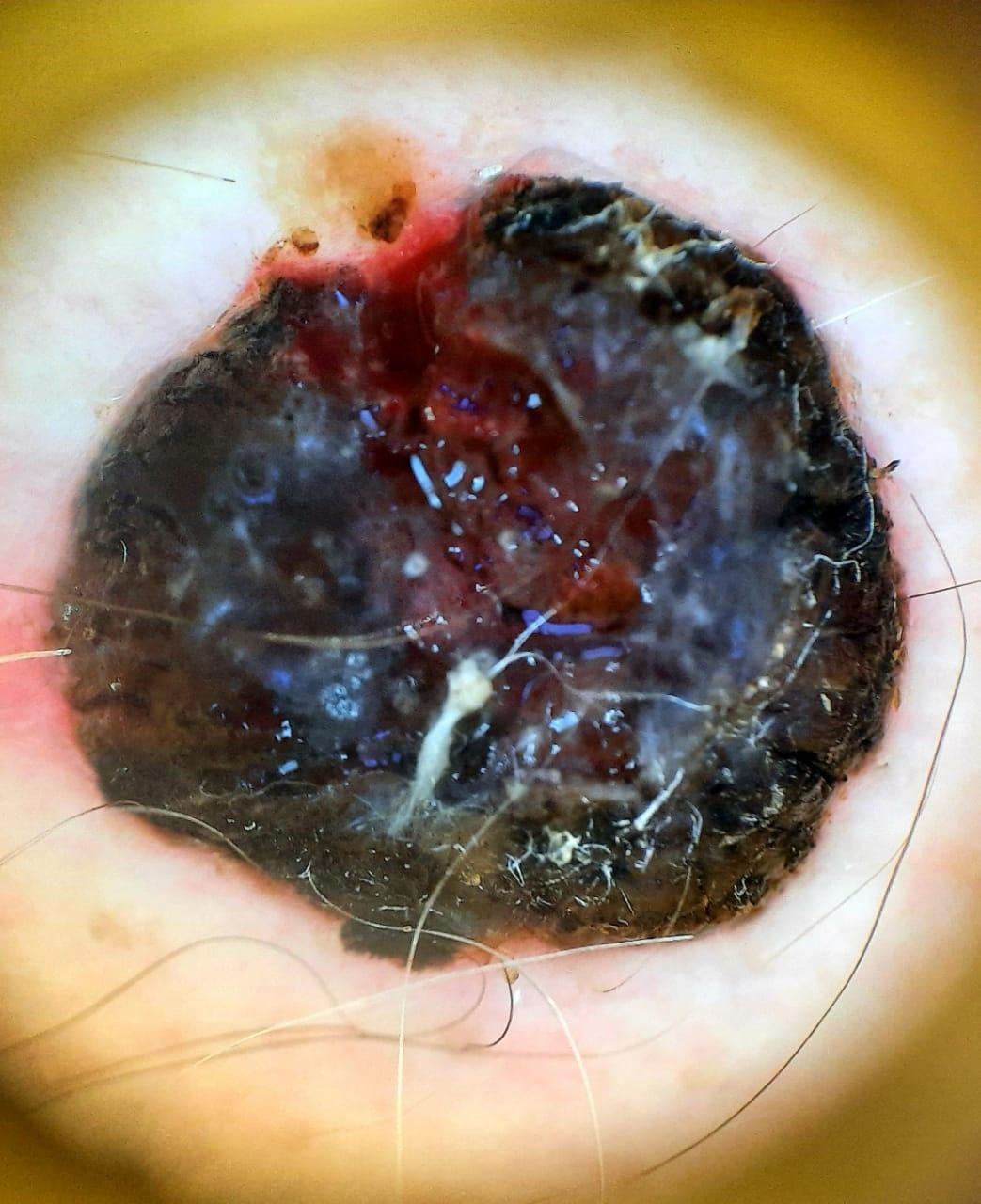A male patient about 75 years old. A dermatoscopic image of a skin lesion. Recorded as Fitzpatrick II. On biopsy, the diagnosis was a skin cancer — a melanoma.